The patient describes having a moderate number of moles. Collected as part of a research study, without a referral diagnosis. The patient reports no personal history of skin cancer:
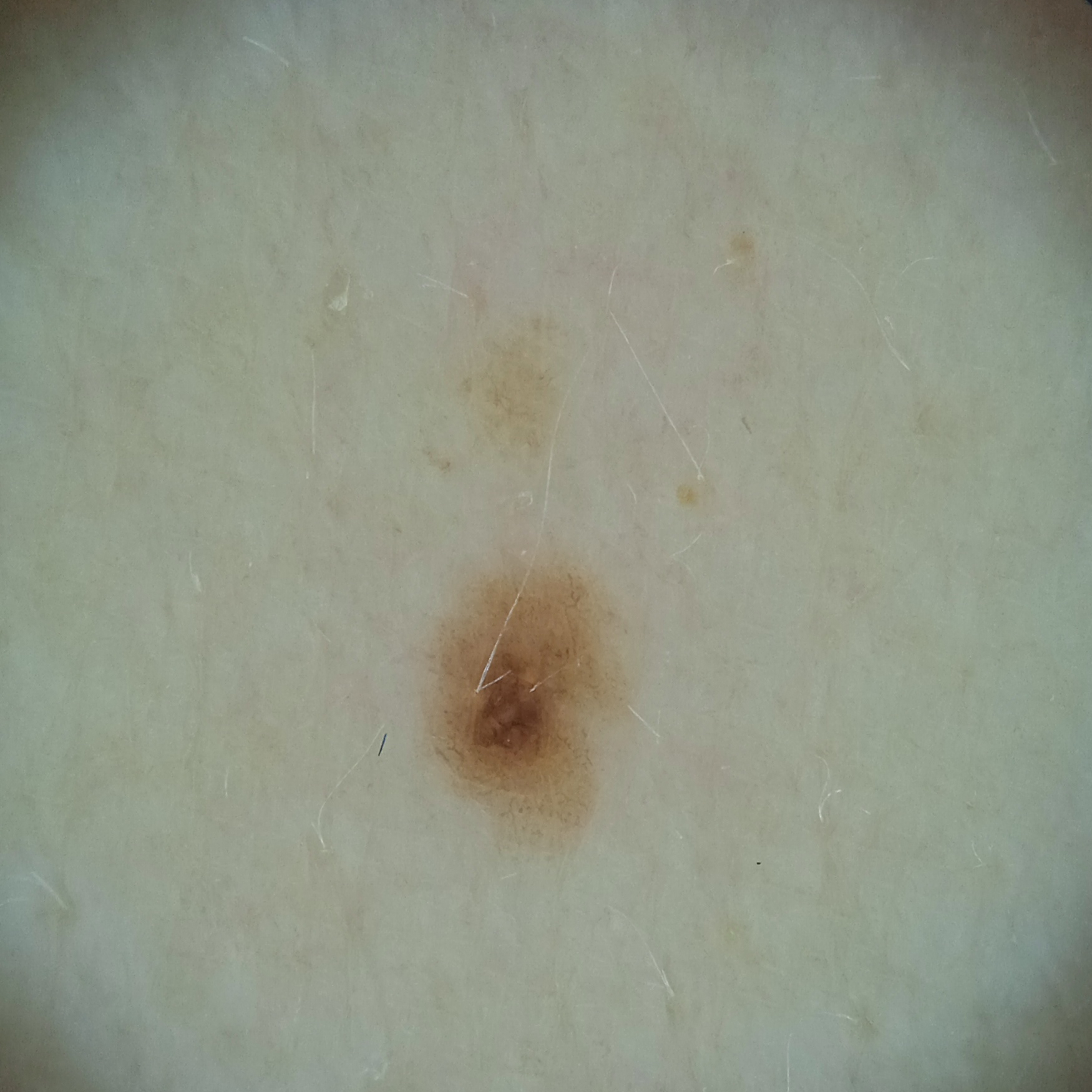Case:
• site: the back
• lesion size: 2.7 mm
• diagnostic label: melanocytic nevus (dermatologist consensus)